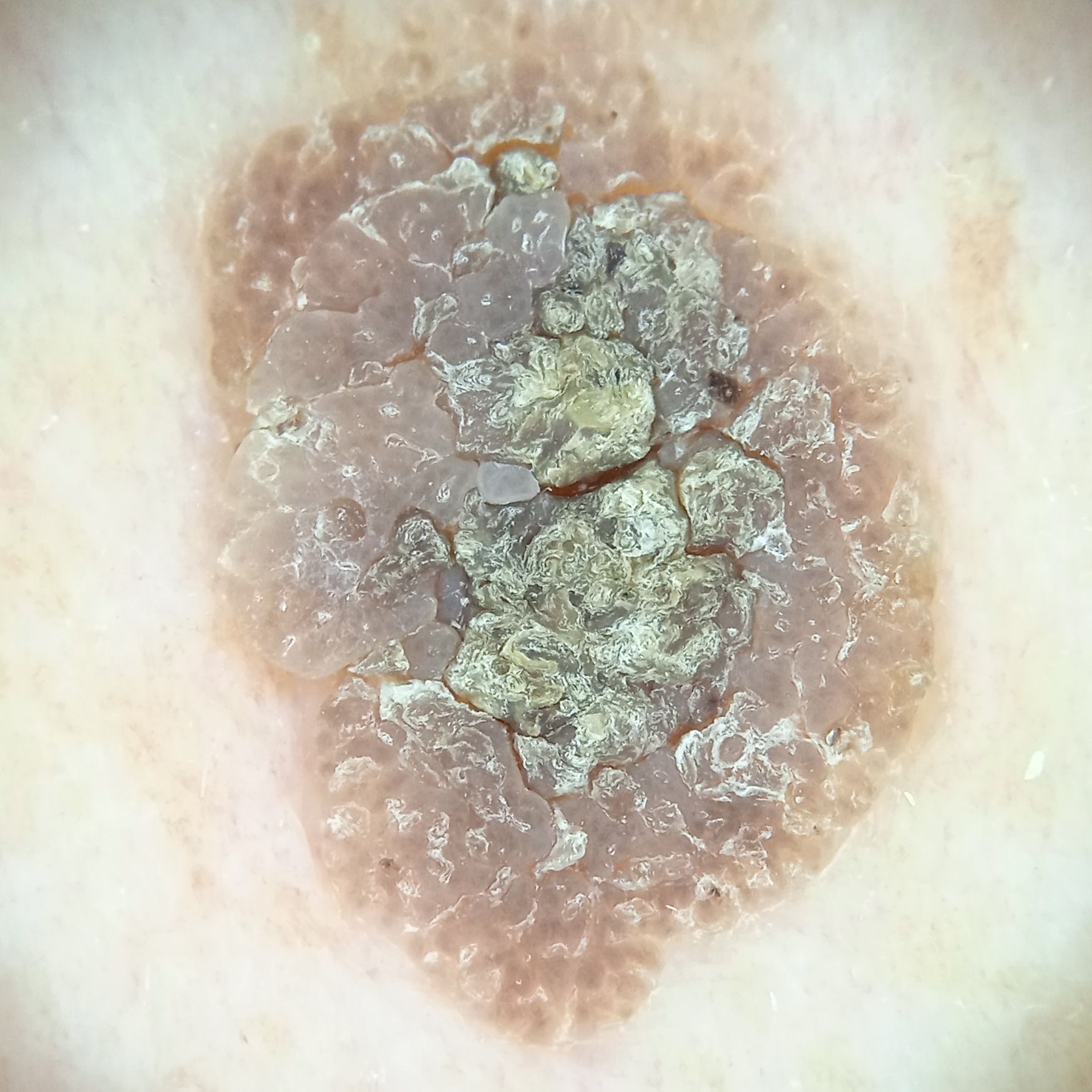Clinical context:
Few moles overall by the patient's own estimate. By self-report, no personal history of cancer. A dermatoscopic image of a skin lesion. Imaged for a research study, with no referral diagnosis recorded. A male patient 62 years old. The patient says their skin reddens with sun exposure. The lesion involves the back. The lesion is about 10.9 mm across.
Impression:
Dermatologist review favored a seborrheic keratosis.